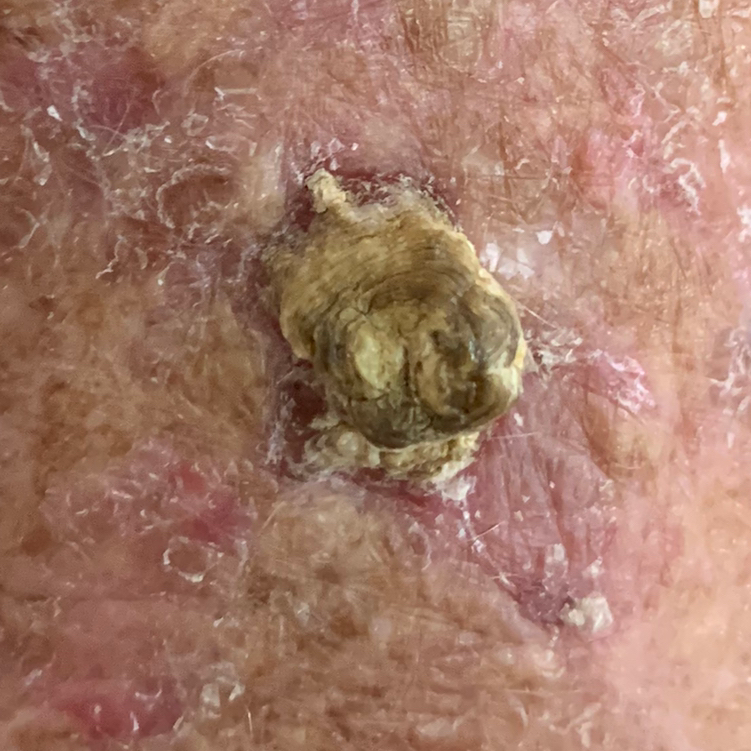Patient and lesion:
A clinical photograph showing a skin lesion. A female patient in their late 70s. The patient is FST II. The lesion measures approximately 10 × 6 mm. Per patient report, the lesion is elevated, hurts, and itches, but has not bled.
Conclusion:
Biopsy-confirmed as an actinic keratosis.